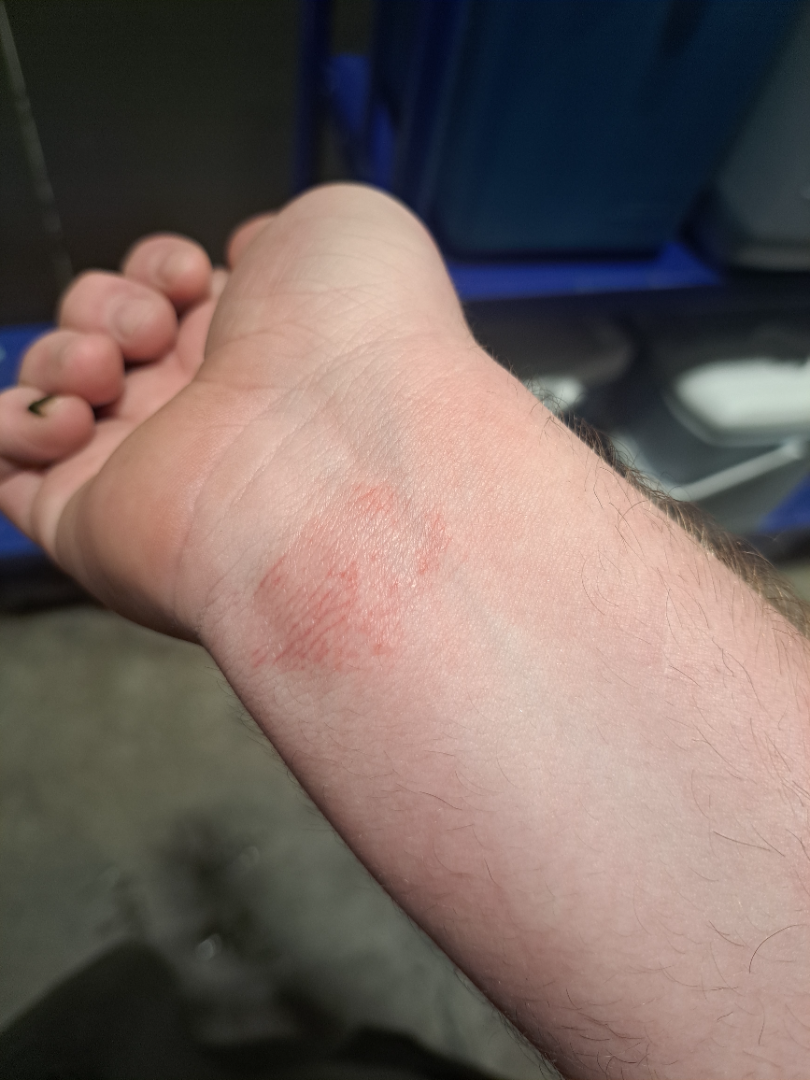Symptoms reported: itching, burning, bothersome appearance and pain. Texture is reported as flat and rough or flaky. The patient considered this a rash. This is a close-up image. Irritant Contact Dermatitis (favored); Allergic Contact Dermatitis (considered).